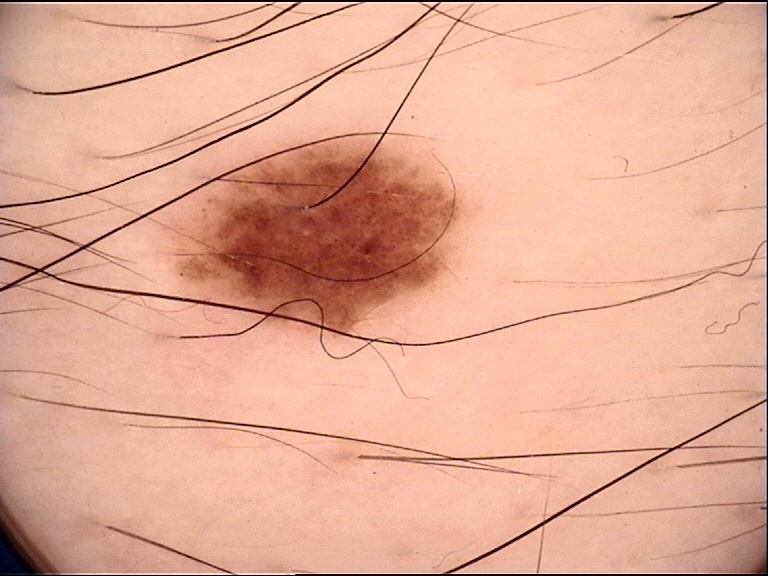class = dysplastic junctional nevus (expert consensus).